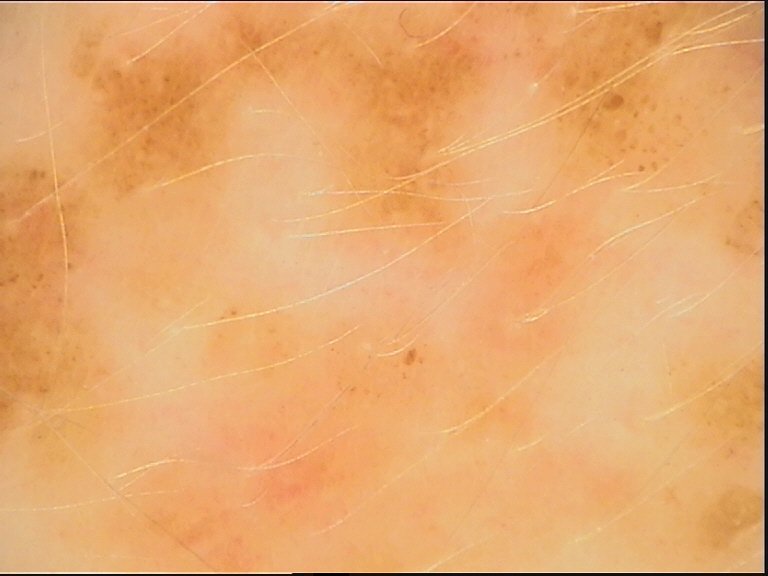modality — dermoscopy; assessment — dysplastic junctional nevus (expert consensus).